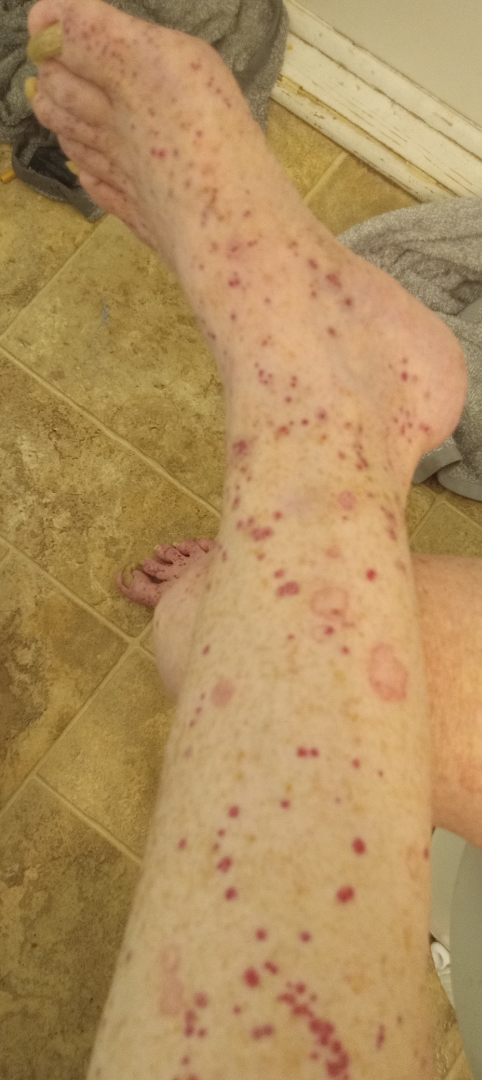Notes:
* anatomic site · leg and back of the torso
* patient describes the issue as · skin that appeared healthy to them
* systemic symptoms · none reported
* described texture · raised or bumpy
* reported symptoms · itching and bothersome appearance
* shot type · close-up
* patient · female, age 60–69
* impression · Leukocytoclastic Vasculitis (most likely)